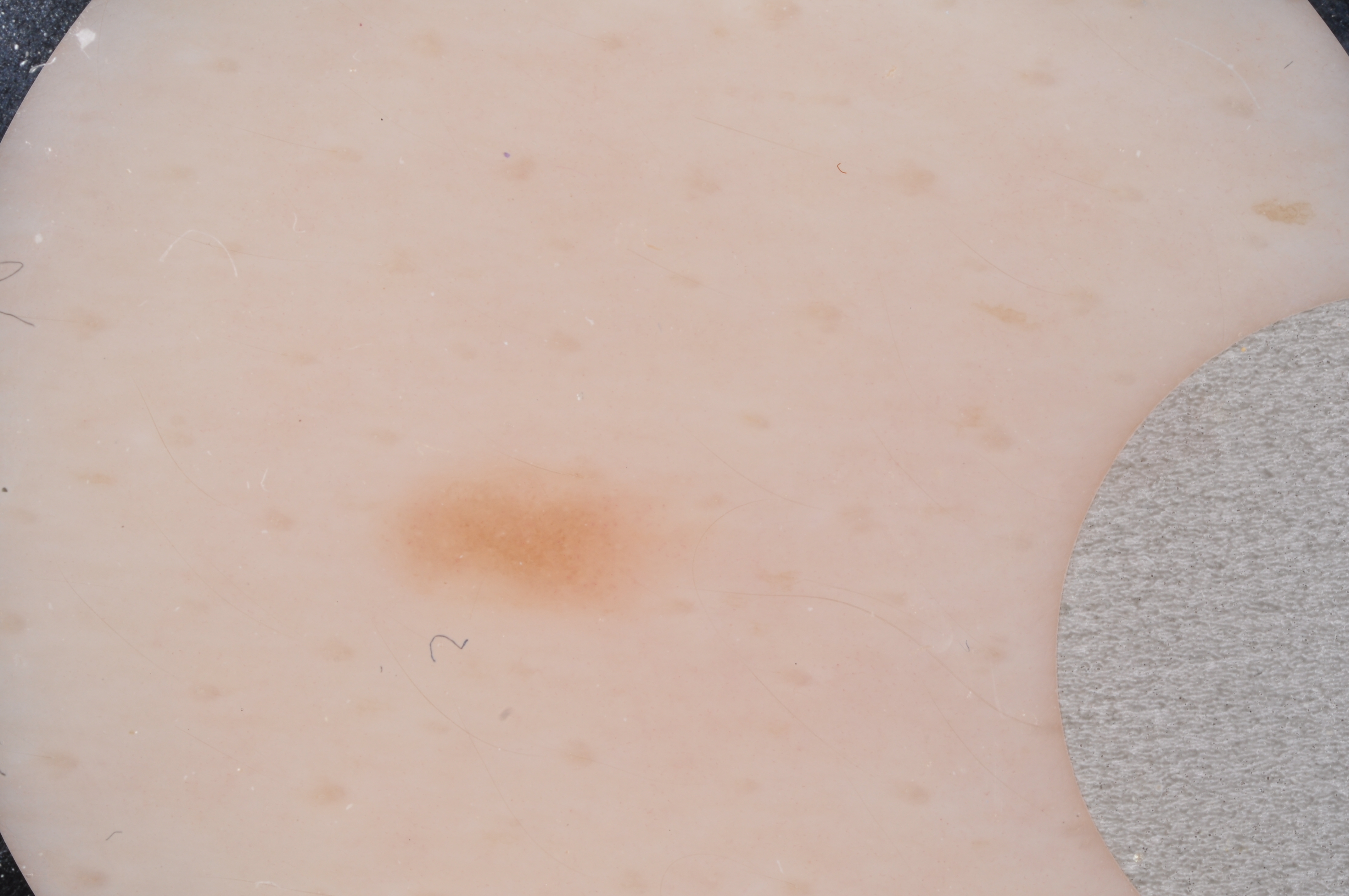Findings: Dermoscopy of a skin lesion. Dermoscopy demonstrates milia-like cysts. The lesion spans <box>368, 462, 708, 629</box>. Conclusion: Clinically diagnosed as a melanocytic nevus.